The contributor is a female aged 18–29 · located on the leg · this is a close-up image.
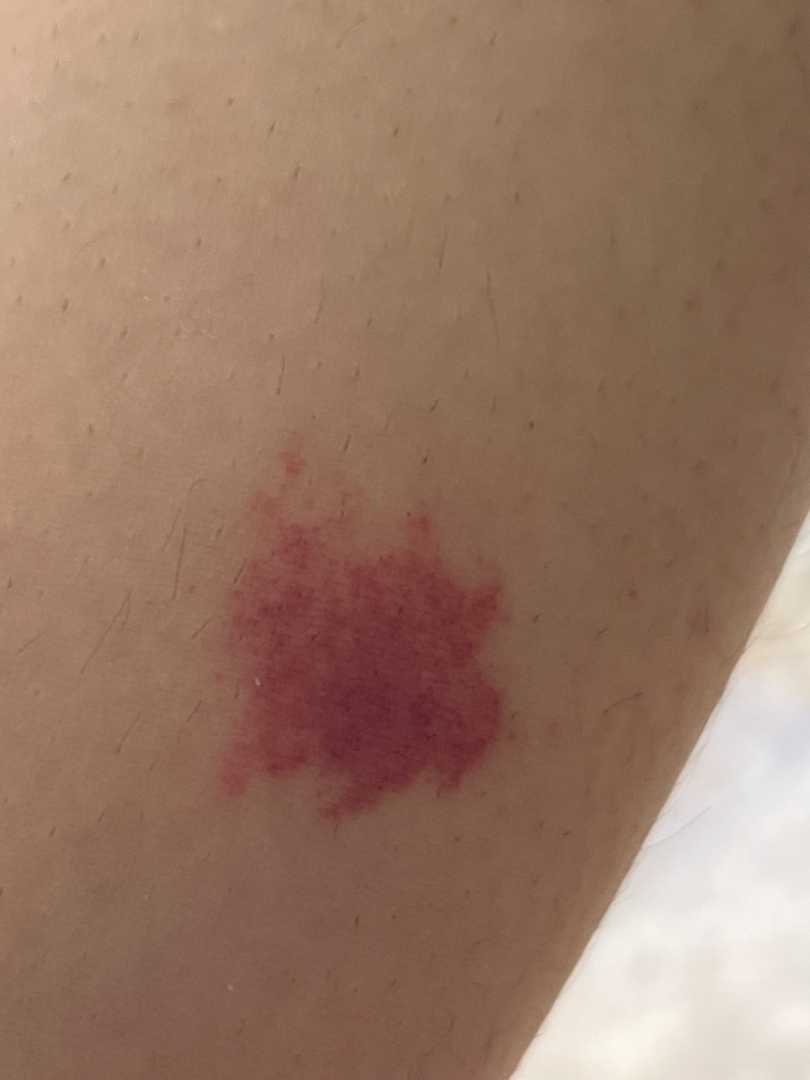<report>
  <texture>flat</texture>
  <patient_category>a rash</patient_category>
  <duration>less than one week</duration>
  <symptoms>itching</symptoms>
  <differential>
    <tied_lead>Hemangioma, Vascular nevus of skin</tied_lead>
    <unlikely>Kaposi's sarcoma of skin</unlikely>
  </differential>
</report>